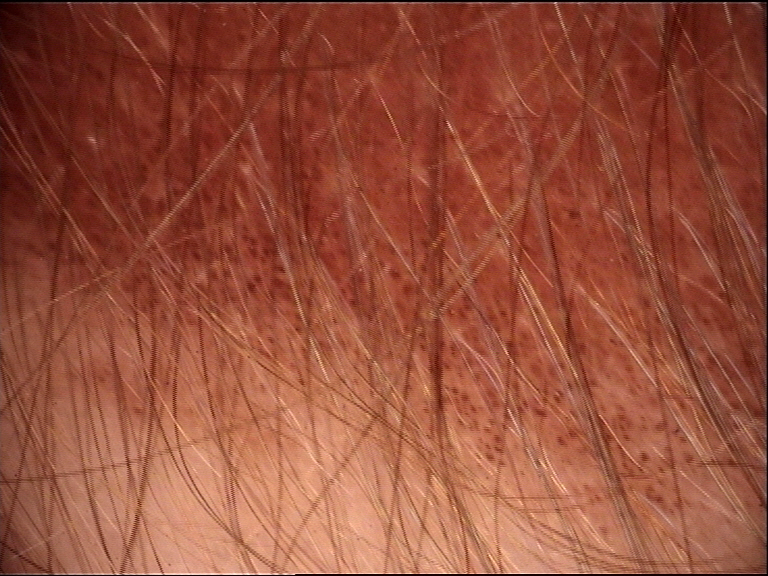<lesion>
  <lesion_type>
    <main_class>banal</main_class>
    <pattern>junctional</pattern>
  </lesion_type>
  <diagnosis>
    <name>congenital junctional nevus</name>
    <code>cjb</code>
    <malignancy>benign</malignancy>
    <super_class>melanocytic</super_class>
    <confirmation>expert consensus</confirmation>
  </diagnosis>
</lesion>